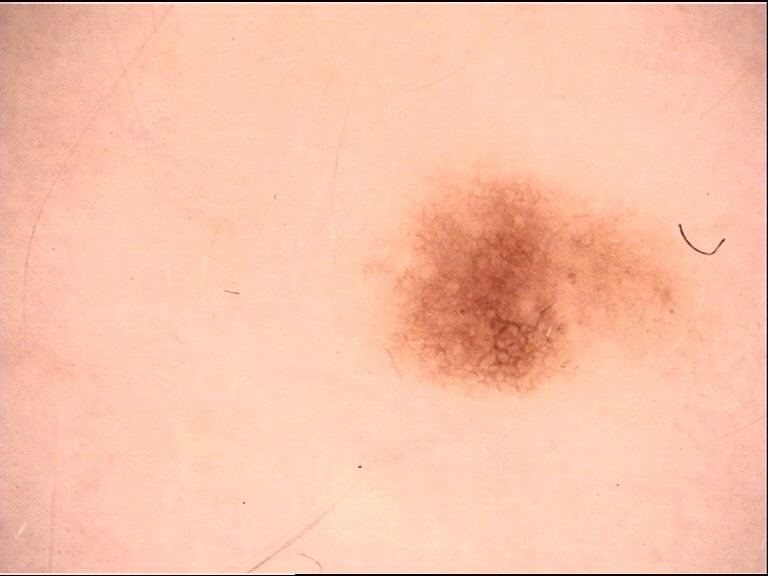Dermoscopy of a skin lesion. The diagnosis was a benign lesion — a dysplastic junctional nevus.